A clinical photograph showing a skin lesion — 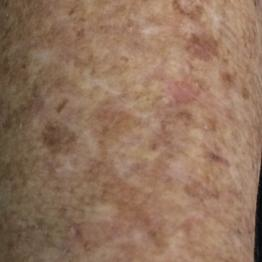The lesion is on a forearm.
The diagnostic impression was an actinic keratosis.